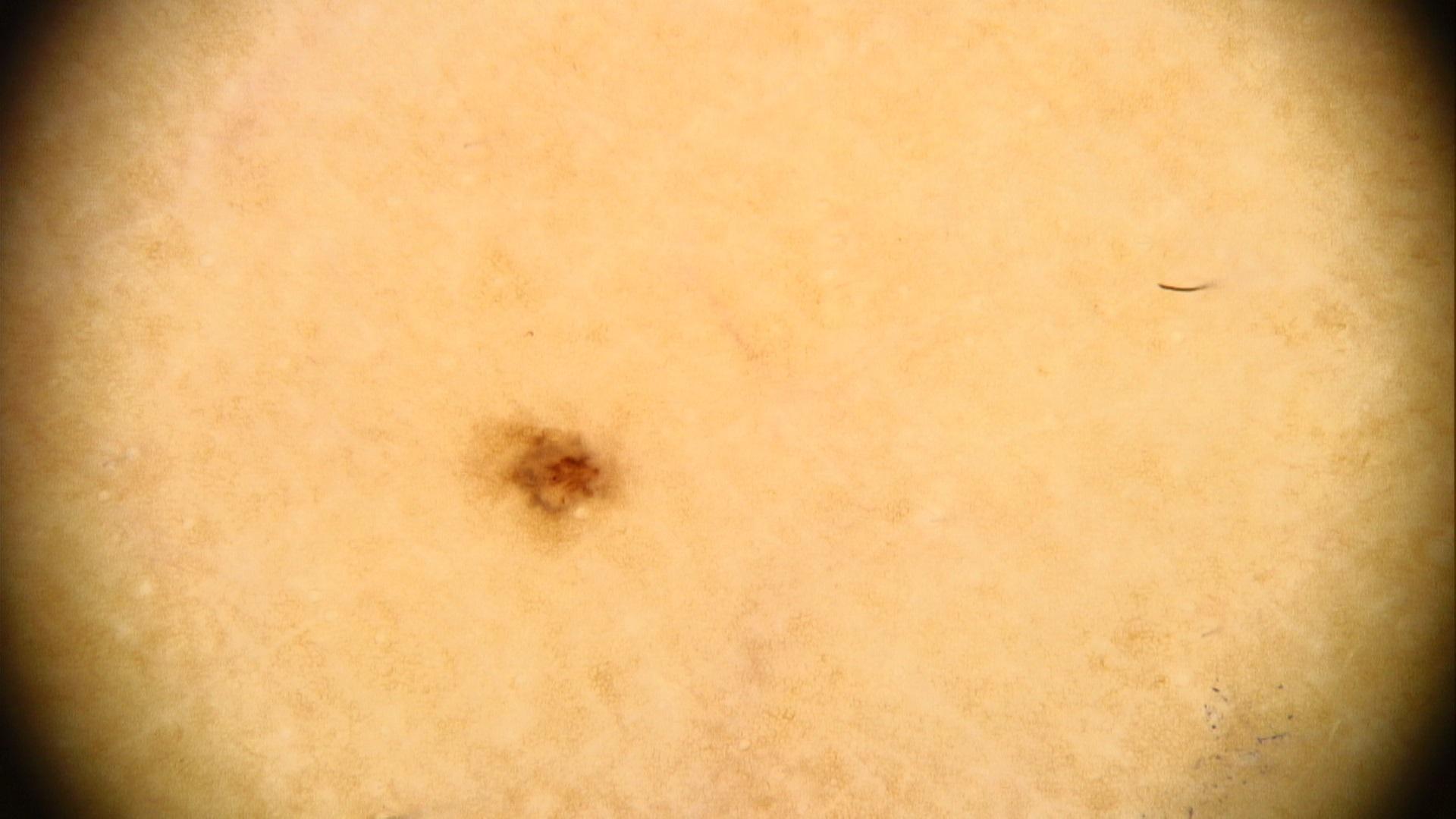Assessment: Clinically diagnosed as a nevus.